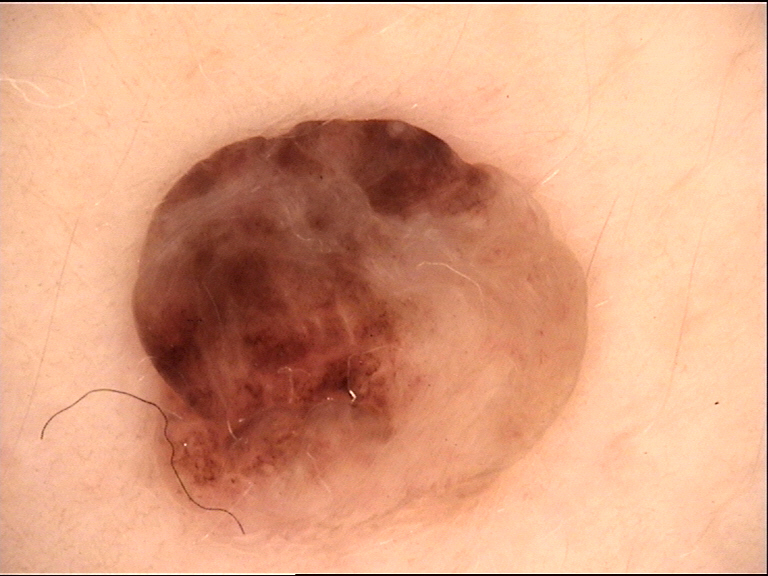A skin lesion imaged with a dermatoscope. The morphology is that of a banal lesion. The diagnosis was a dermal nevus.